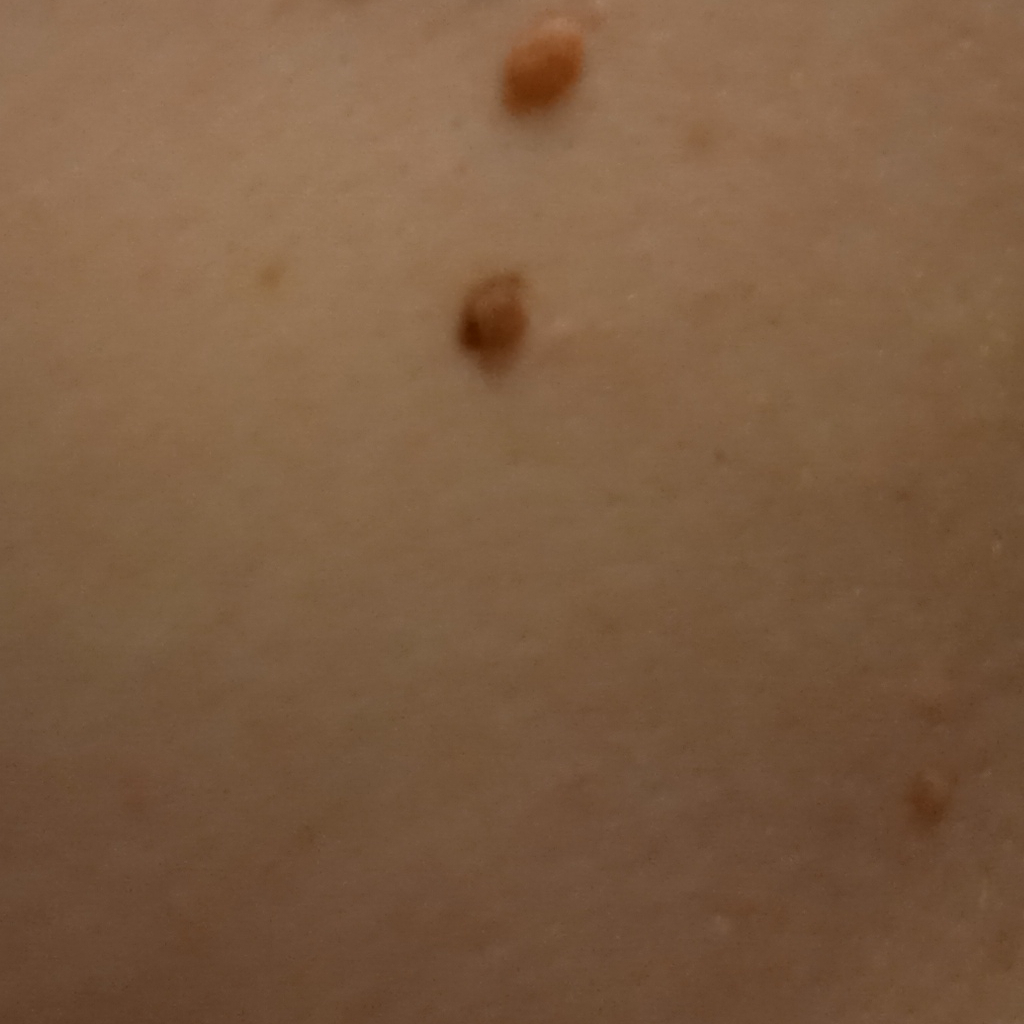{"mole_burden": "numerous melanocytic nevi", "image": "clinical photograph", "referral": "research study (no referral diagnosis)", "patient": {"age": 26, "sex": "female"}, "sun_reaction": "skin reddens with sun exposure", "lesion_size": {"diameter_mm": 4.5}, "diagnosis": {"name": "melanocytic nevus", "malignancy": "benign"}}